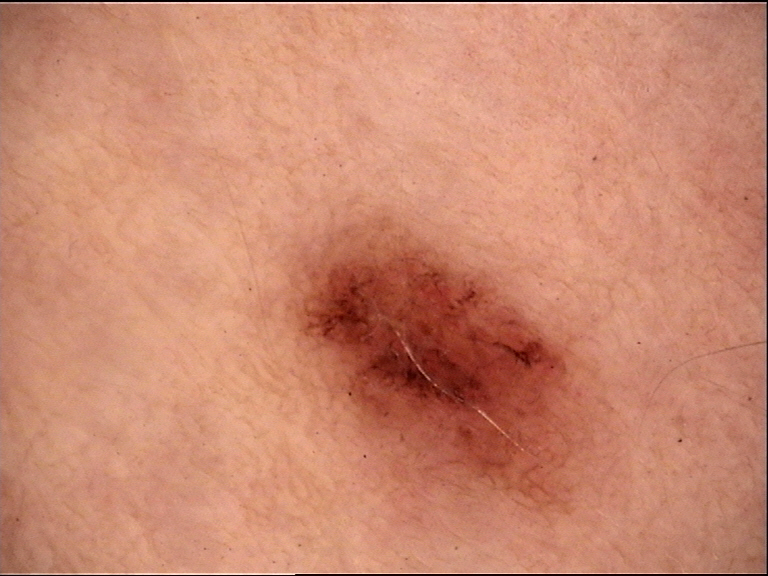A dermoscopic photograph of a skin lesion. Diagnosed as a benign lesion — a dysplastic junctional nevus.